A female patient, aged around 50. A skin lesion imaged with a dermatoscope — 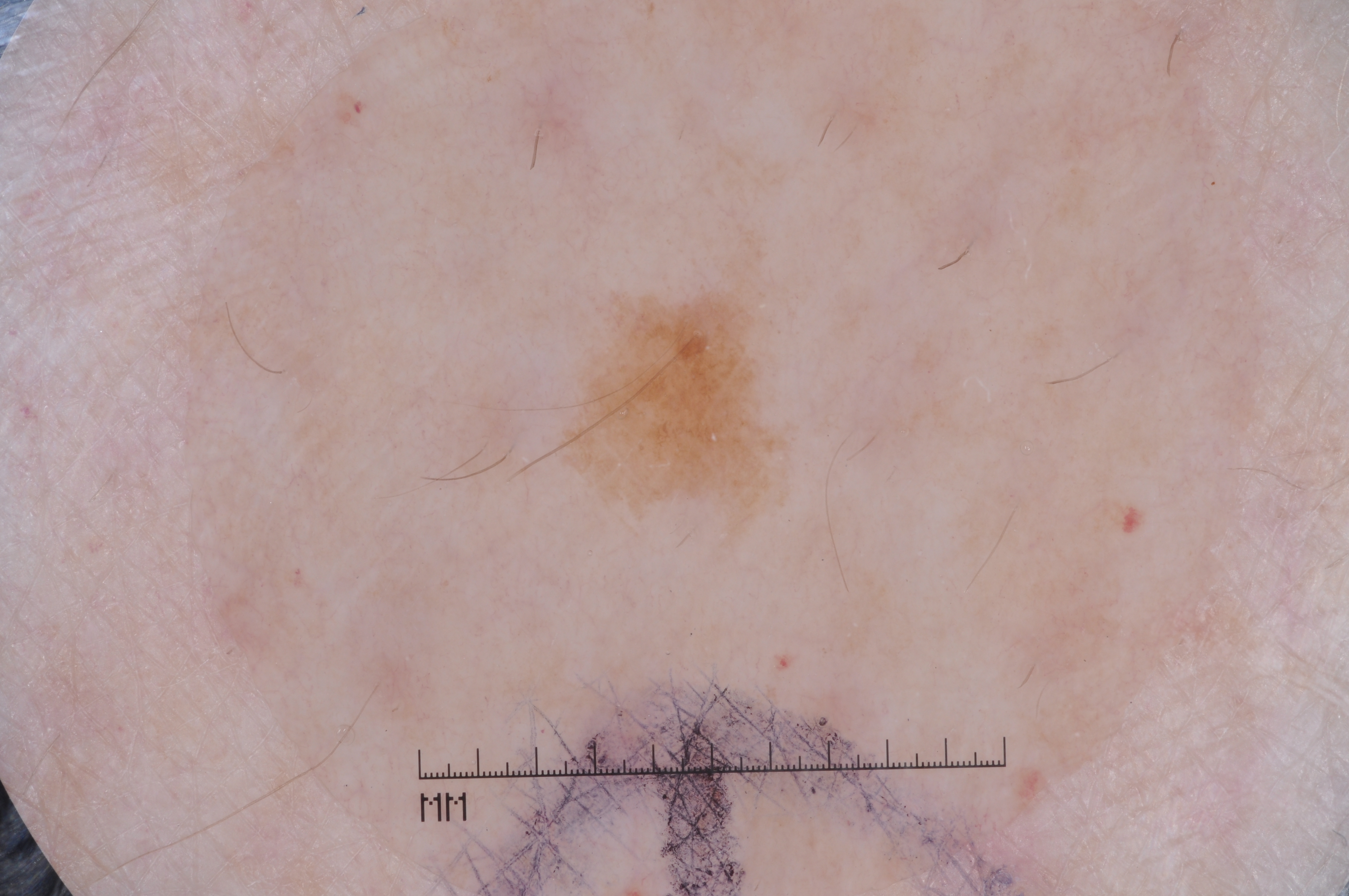Findings: The lesion occupies the region 580, 301, 769, 497. On dermoscopy, the lesion shows milia-like cysts, with no streaks, negative network, or pigment network. The lesion takes up about 2% of the image. Assessment: Clinically diagnosed as a seborrheic keratosis, a benign skin lesion.